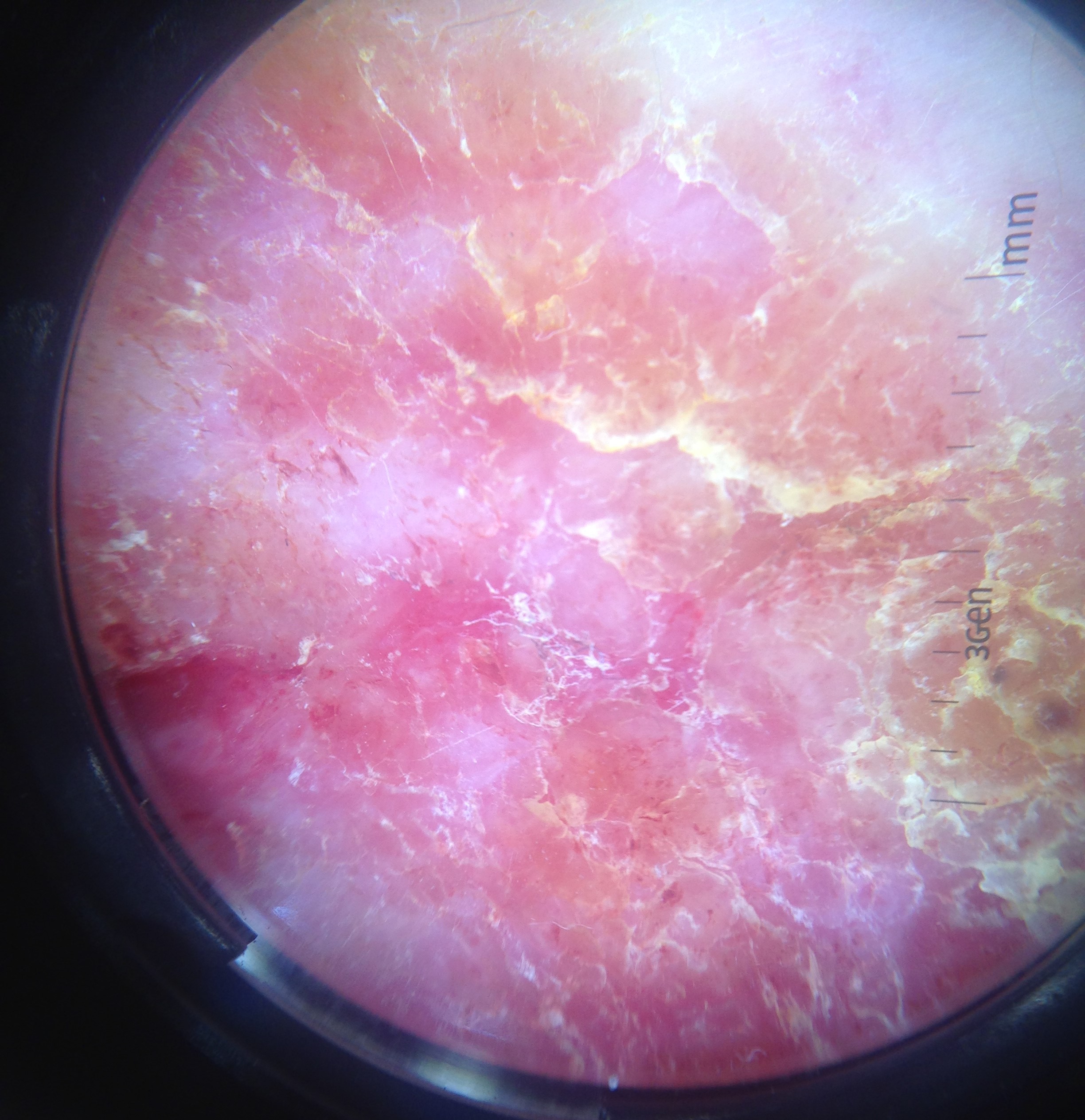image: dermoscopy
lesion_type:
  main_class: keratinocytic
diagnosis:
  name: Bowen's disease
  code: bd
  malignancy: malignant
  super_class: non-melanocytic
  confirmation: histopathology